A skin lesion imaged with a dermatoscope.
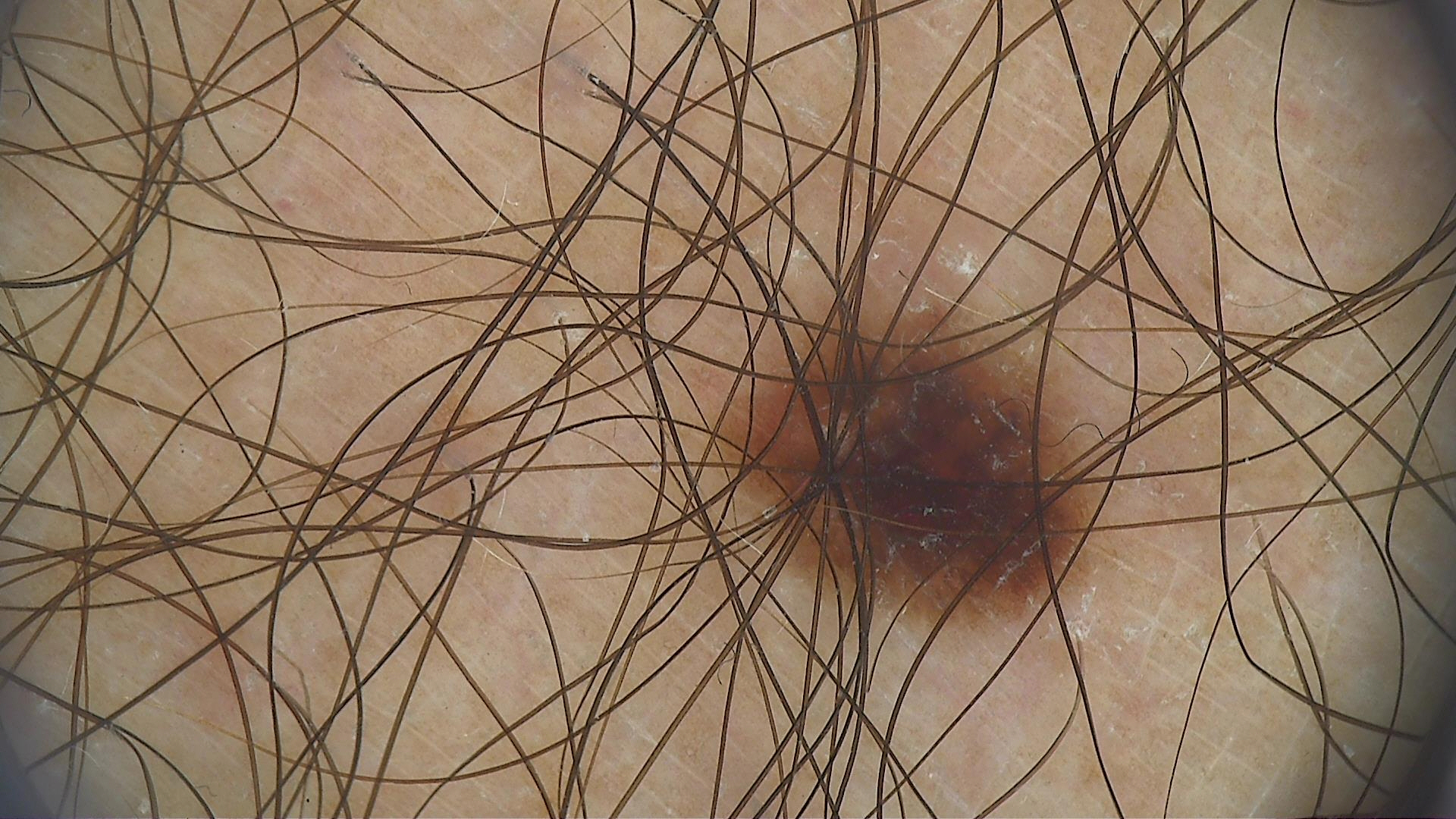label — dysplastic junctional nevus (expert consensus).